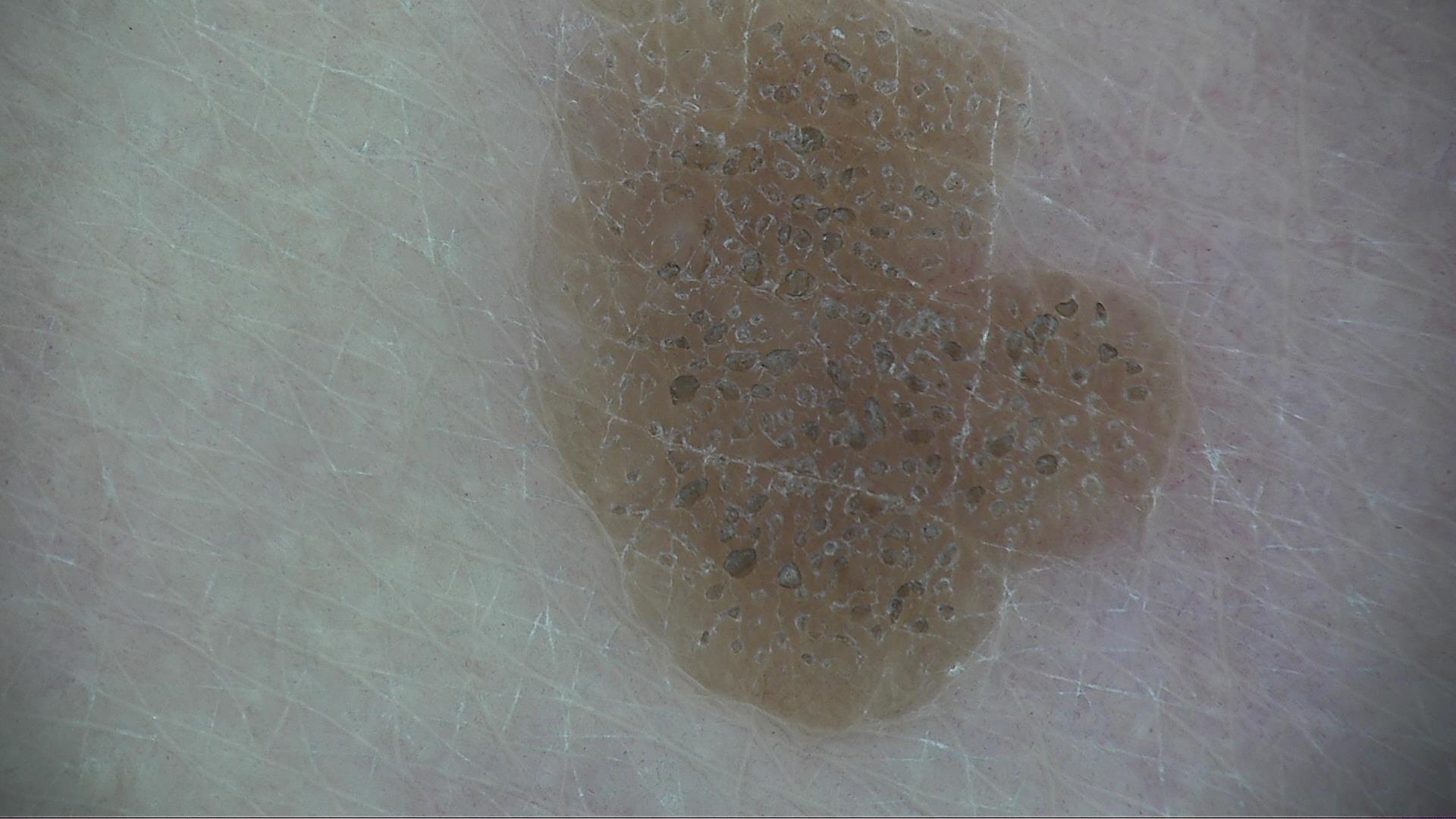Case:
A dermoscopic image of a skin lesion.
Conclusion:
The diagnostic label was a keratinocytic lesion — a seborrheic keratosis.